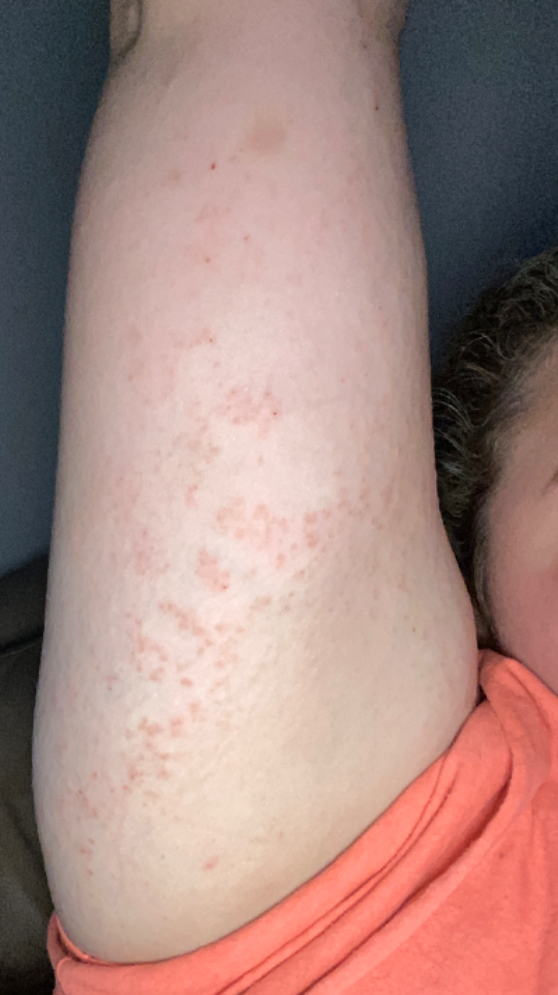The lesion involves the arm, back of the torso, head or neck, leg and front of the torso.
Female contributor, age 18–29.
An image taken at a distance.
Most likely Allergic Contact Dermatitis; with consideration of Keratosis pilaris; possibly Eczema.